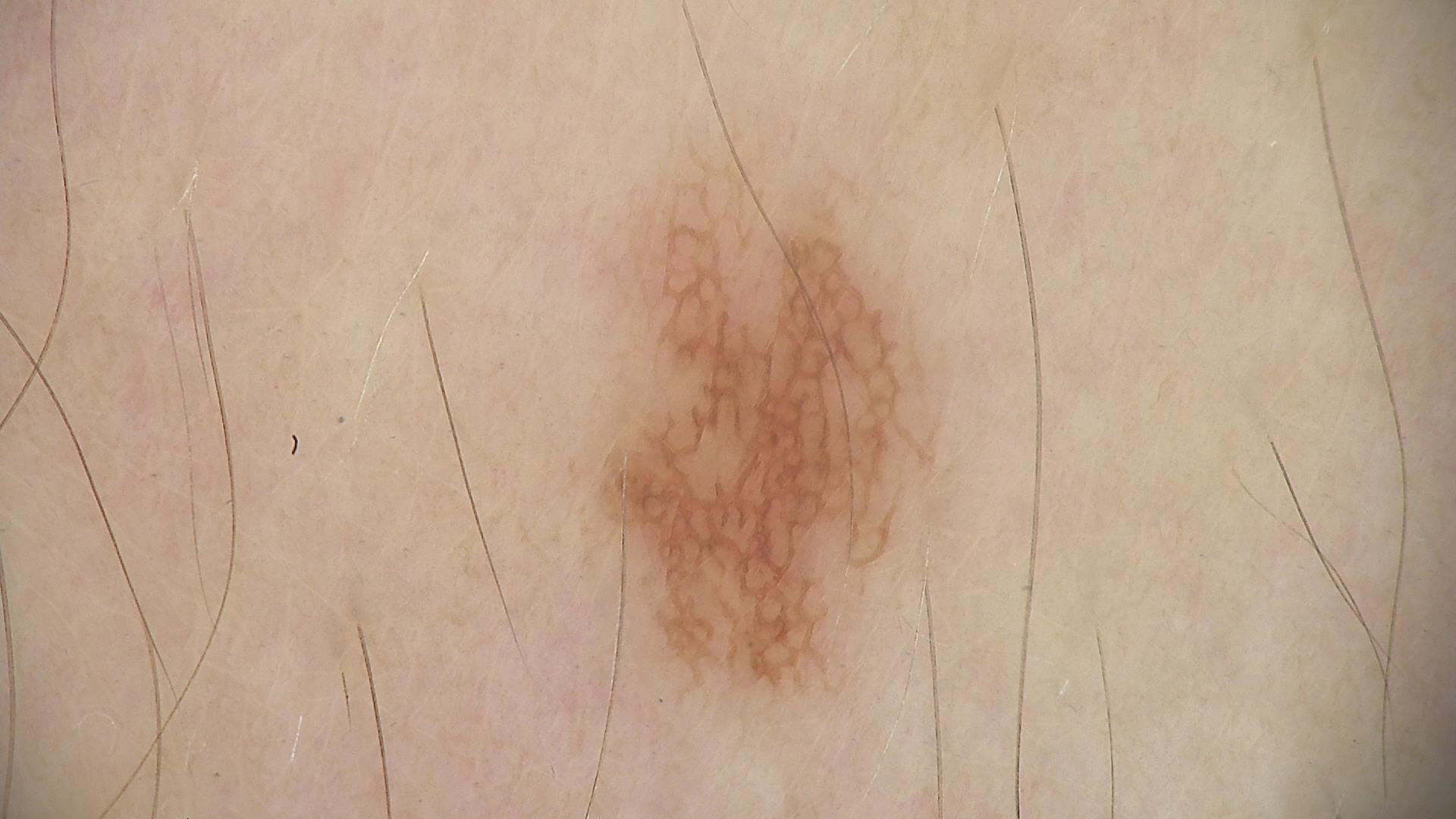The diagnosis was a dysplastic junctional nevus.